The contributor is female · the lesion involves the arm · close-up view.
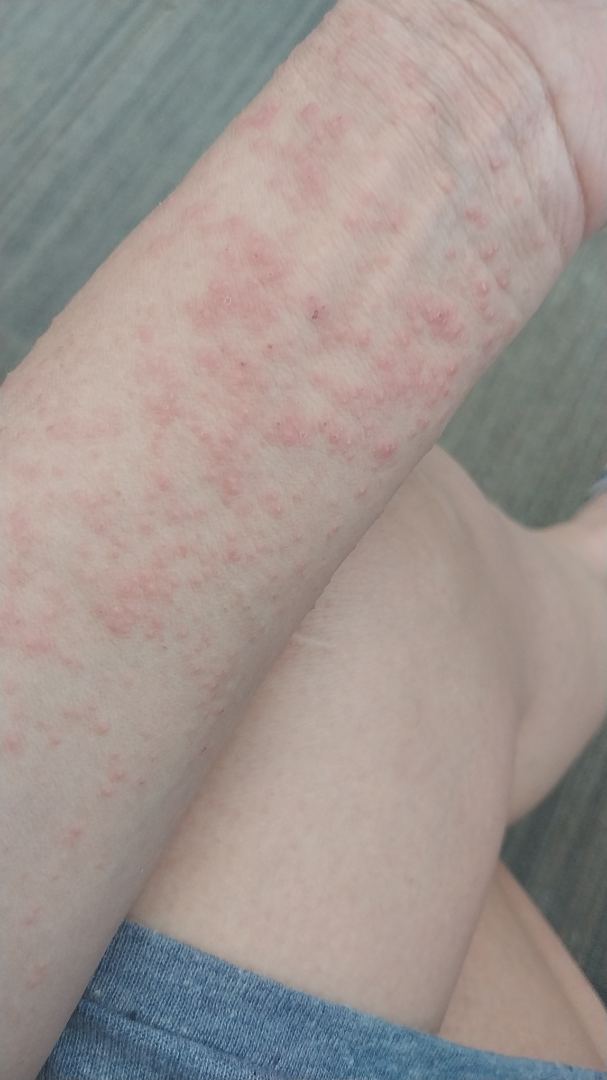Case summary:
* impression — the differential, in no particular order, includes Contact dermatitis and Eczema; also consider Dermatitis herpetiformis